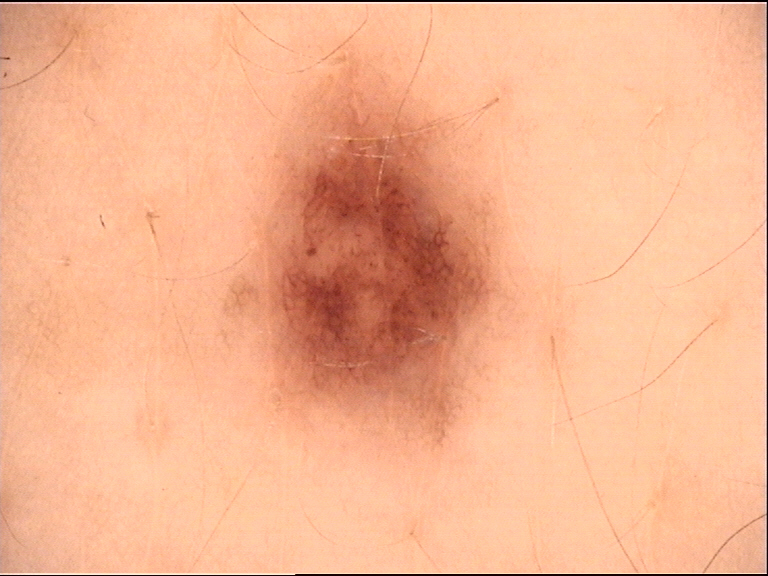<dermoscopy>
  <image>dermatoscopy</image>
  <diagnosis>
    <name>dysplastic junctional nevus</name>
    <code>jd</code>
    <malignancy>benign</malignancy>
    <super_class>melanocytic</super_class>
    <confirmation>expert consensus</confirmation>
  </diagnosis>
</dermoscopy>